Dermoscopy of a skin lesion.
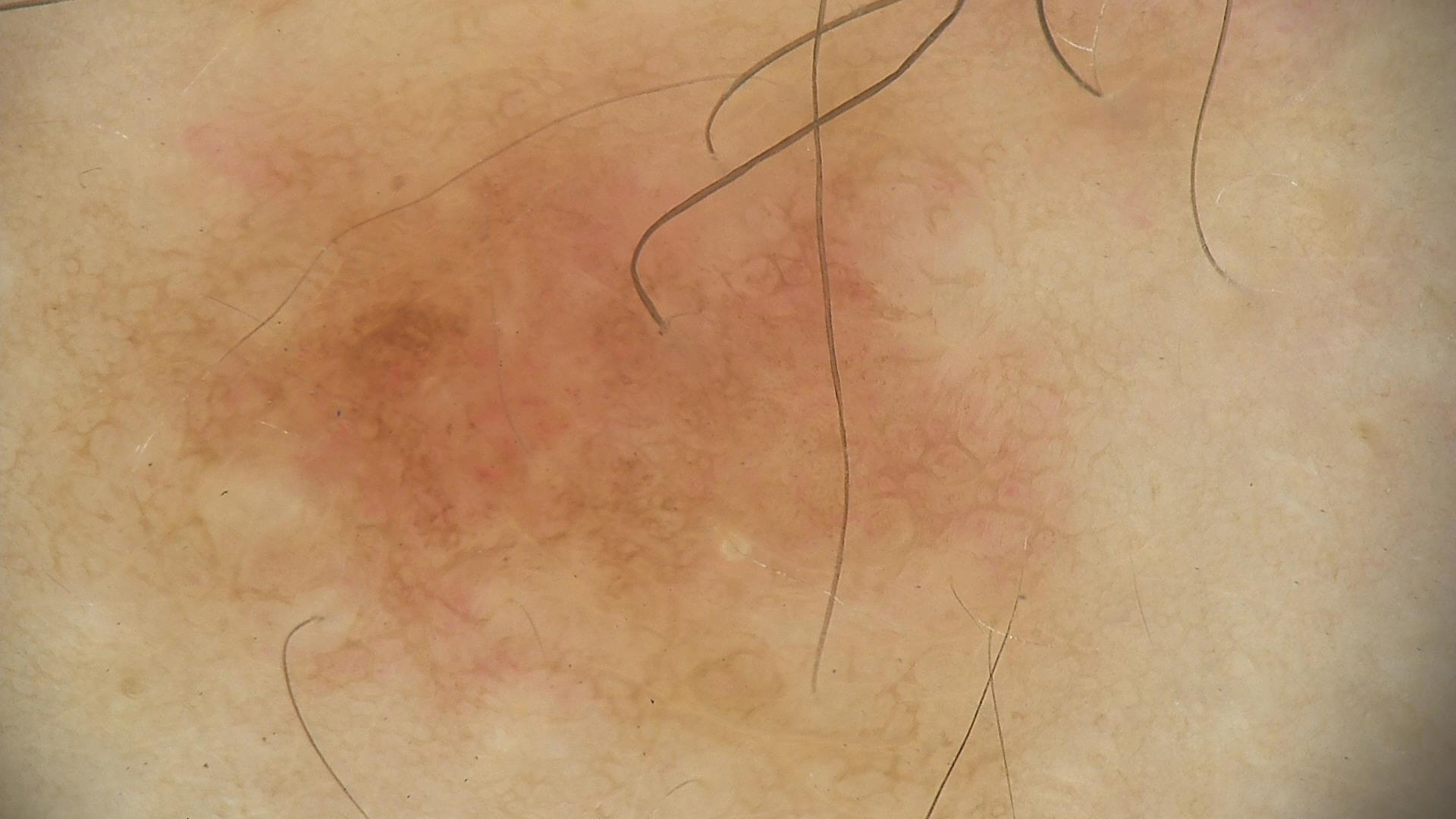label=dysplastic junctional nevus (expert consensus).